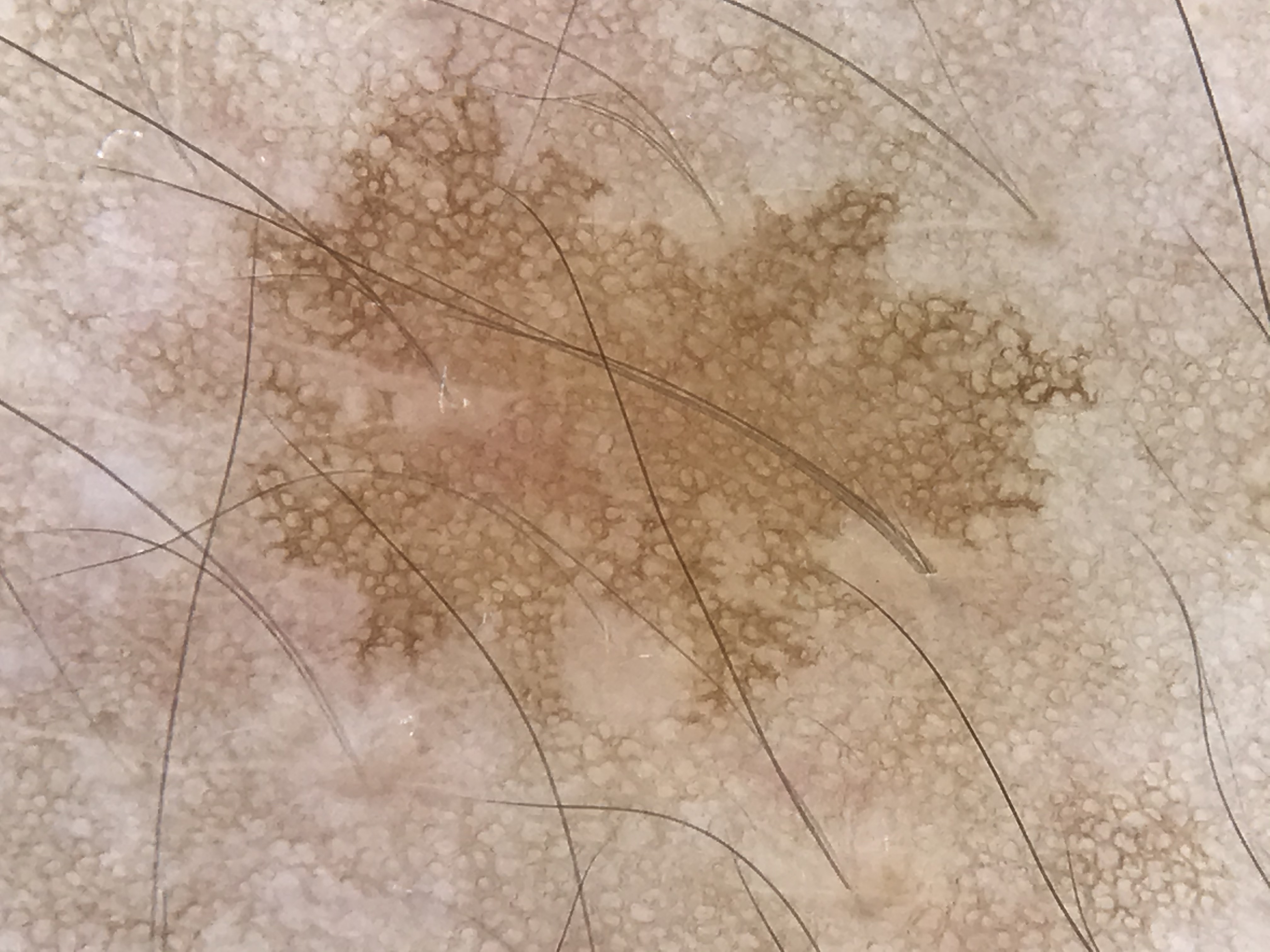A dermoscopic close-up of a skin lesion. Classified as a solar lentigo.